Self-categorized by the patient as a pigmentary problem; located on the leg; reported duration is three to twelve months; the contributor is 40–49, male; an image taken at an angle; the lesion is associated with bothersome appearance and darkening; the lesion is described as flat: 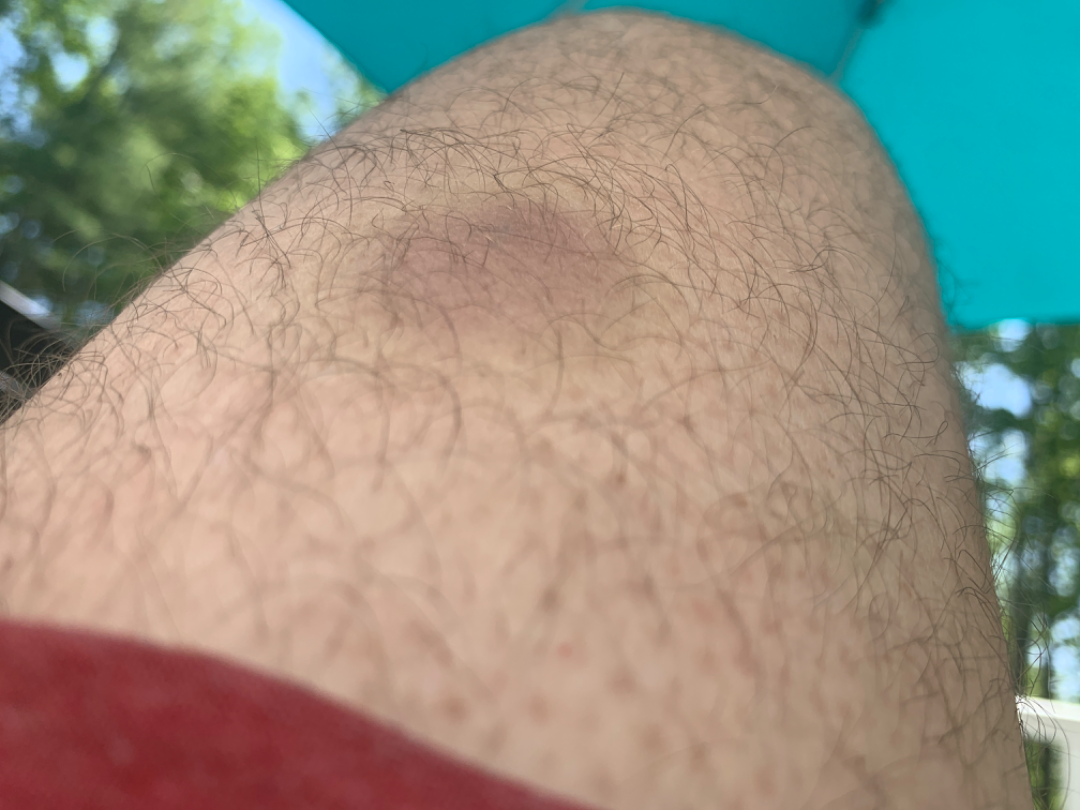On remote review of the image: the favored diagnosis is Drug Rash; an alternative is ecchymoses.